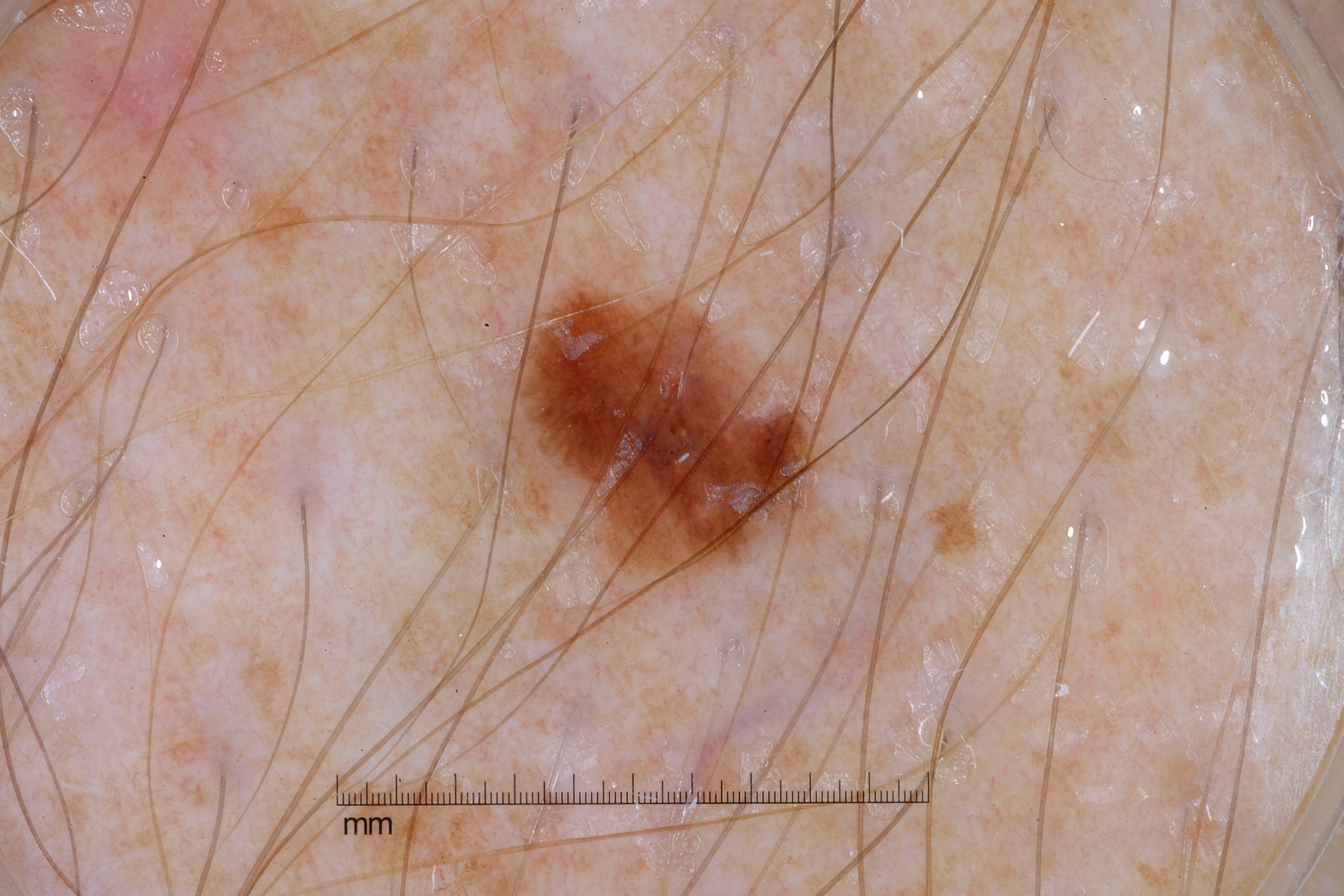patient = male, about 60 years old | image = dermoscopic image | features = milia-like cysts and pigment network; absent: streaks and negative network | lesion location = bbox(525, 294, 818, 574) | impression = a melanocytic nevus.